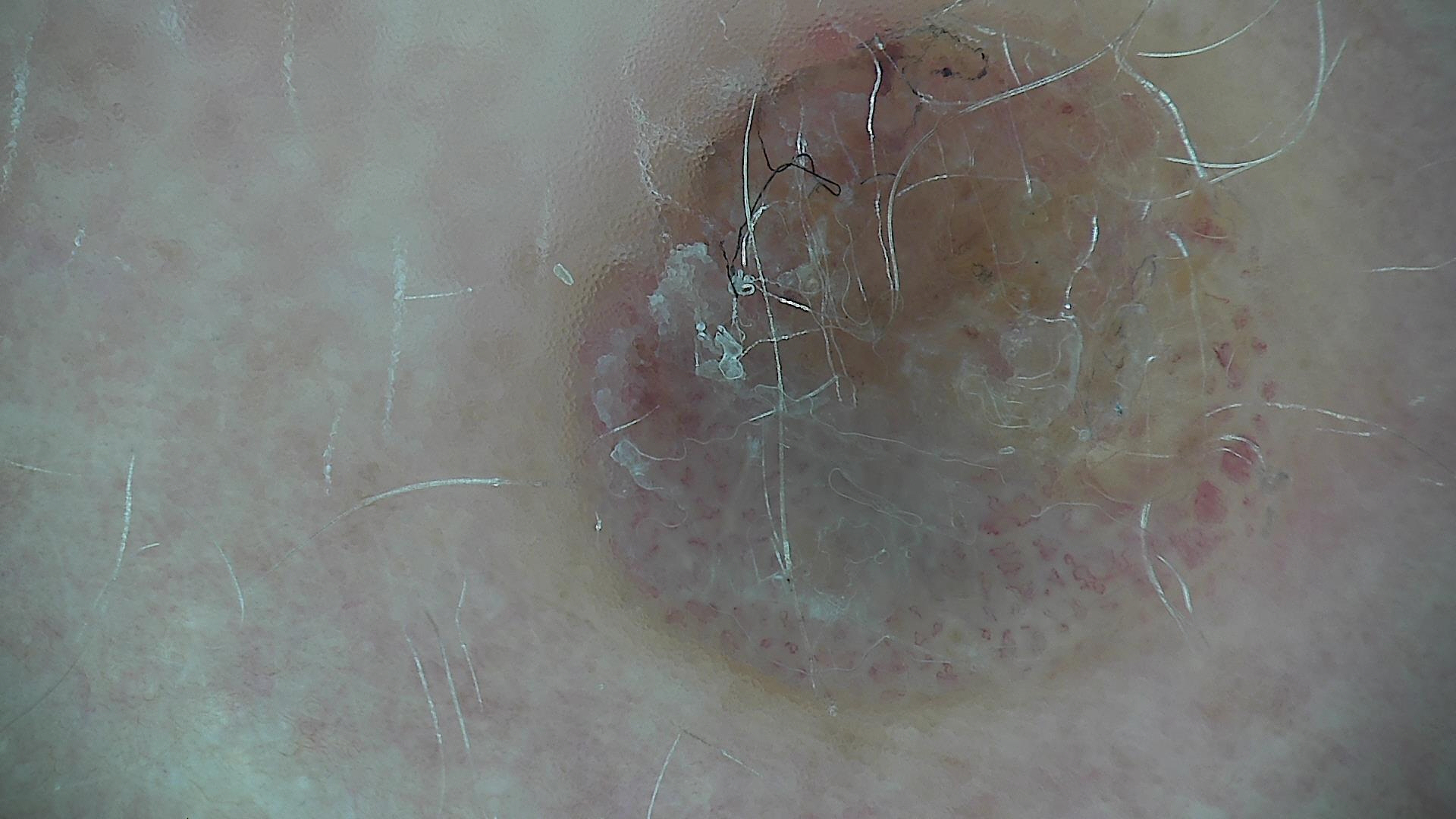Findings:
A dermoscopic image of a skin lesion. The architecture is that of a fibro-histiocytic lesion.
Conclusion:
The diagnosis was a benign lesion — a dermatofibroma.